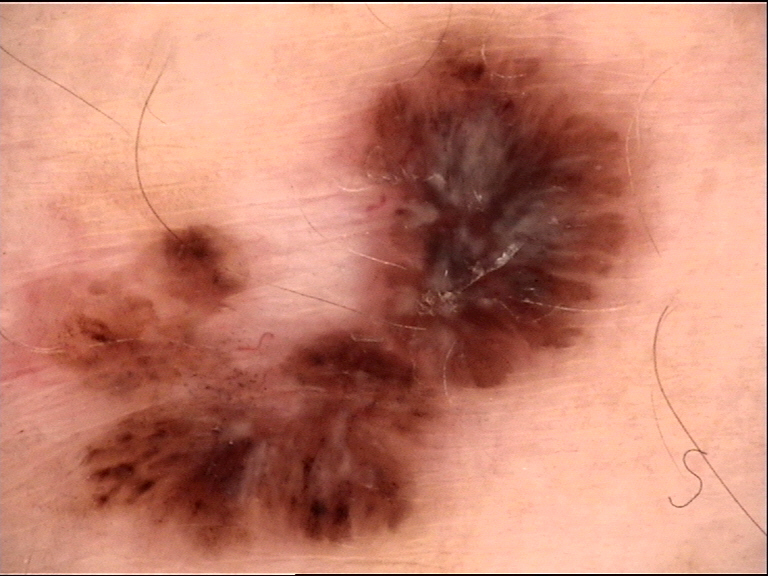<dermoscopy>
  <diagnosis>
    <name>basal cell carcinoma</name>
    <code>bcc</code>
    <malignancy>malignant</malignancy>
    <super_class>non-melanocytic</super_class>
    <confirmation>histopathology</confirmation>
  </diagnosis>
</dermoscopy>